Contact-polarized dermoscopy of a skin lesion. The patient is FST II. A female patient about 60 years old — 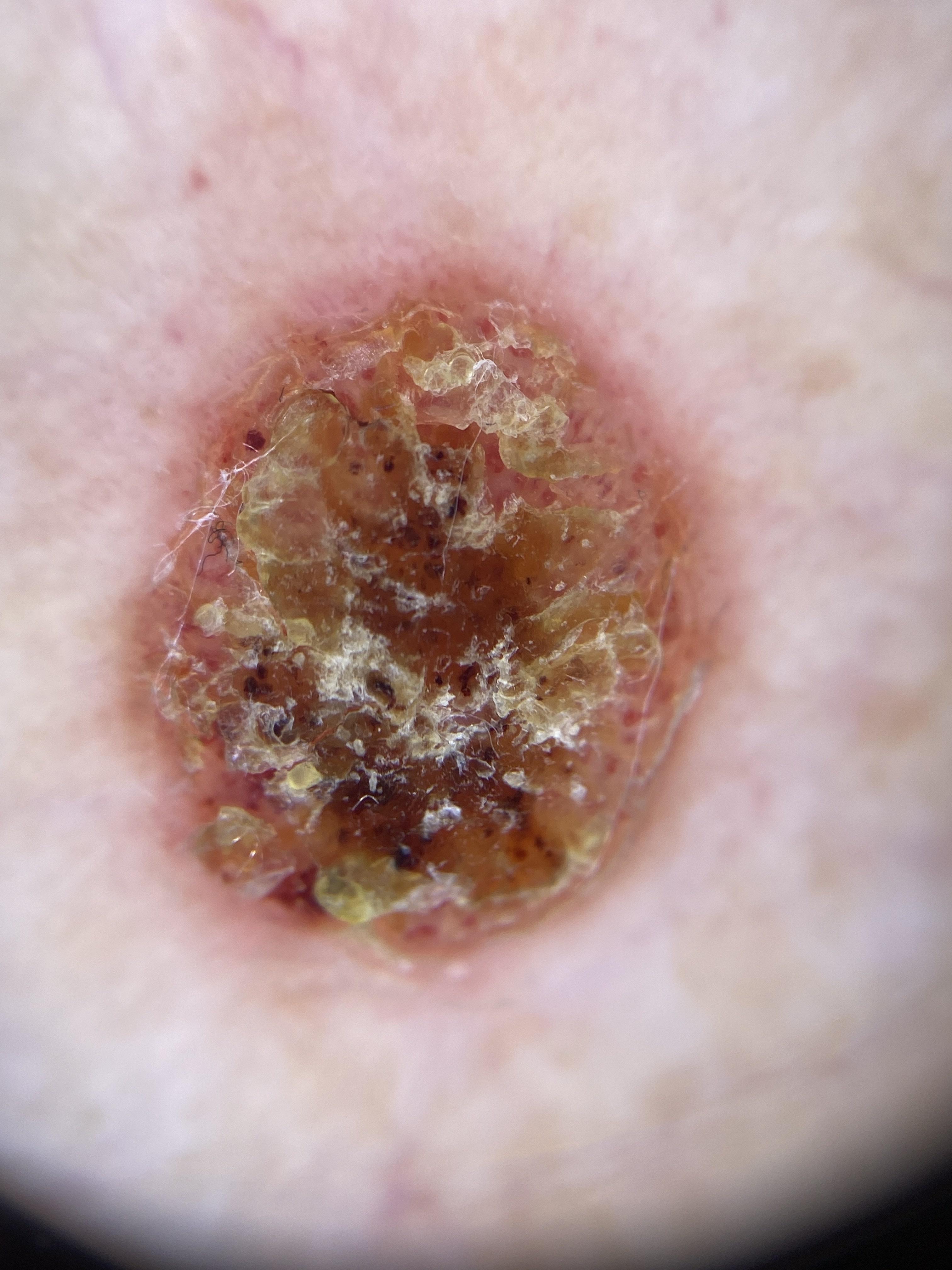location=a lower extremity | pathology=Seborrheic keratosis (biopsy-proven).